A patient aged 48; a clinical photograph showing a skin lesion — 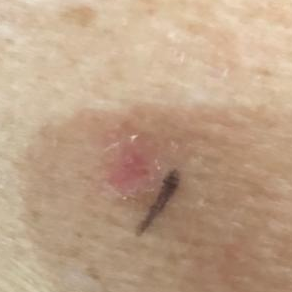Q: What symptoms does the patient report?
A: itching
Q: What is this lesion?
A: actinic keratosis (clinical consensus)